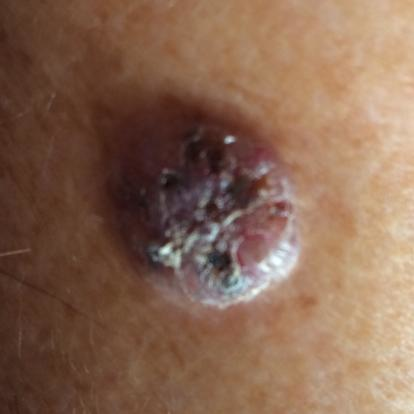Findings: A male subject in their early 70s. A clinical close-up photograph of a skin lesion. The lesion involves an arm. Conclusion: The biopsy diagnosis was a basal cell carcinoma.